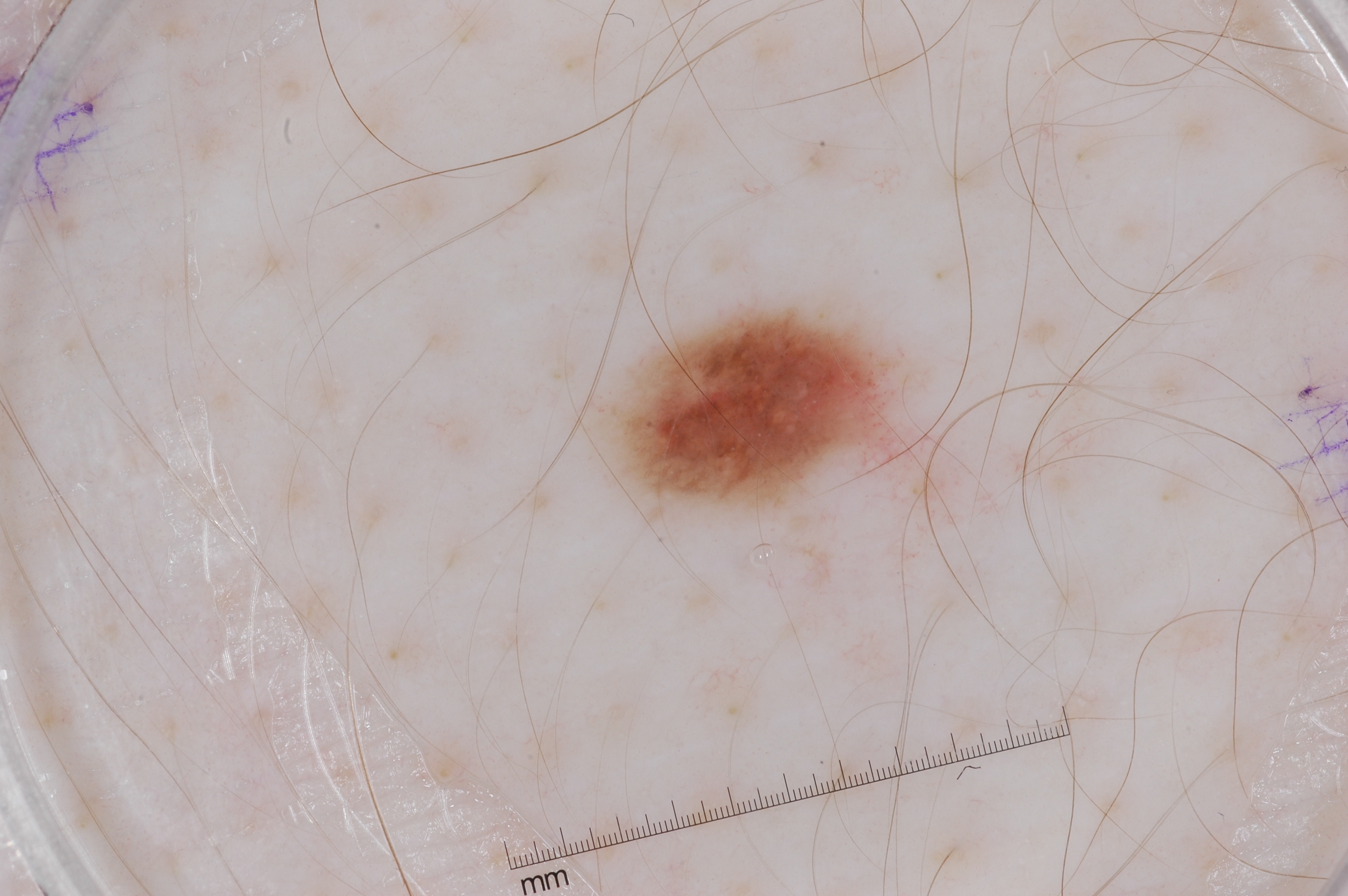Case summary: A dermoscopic image of a skin lesion. On dermoscopy, the lesion shows pigment network. With coordinates (x1, y1, x2, y2), the lesion is bounded by [604, 290, 919, 530]. Impression: Consistent with a melanocytic nevus.